A dermoscopic photograph of a skin lesion:
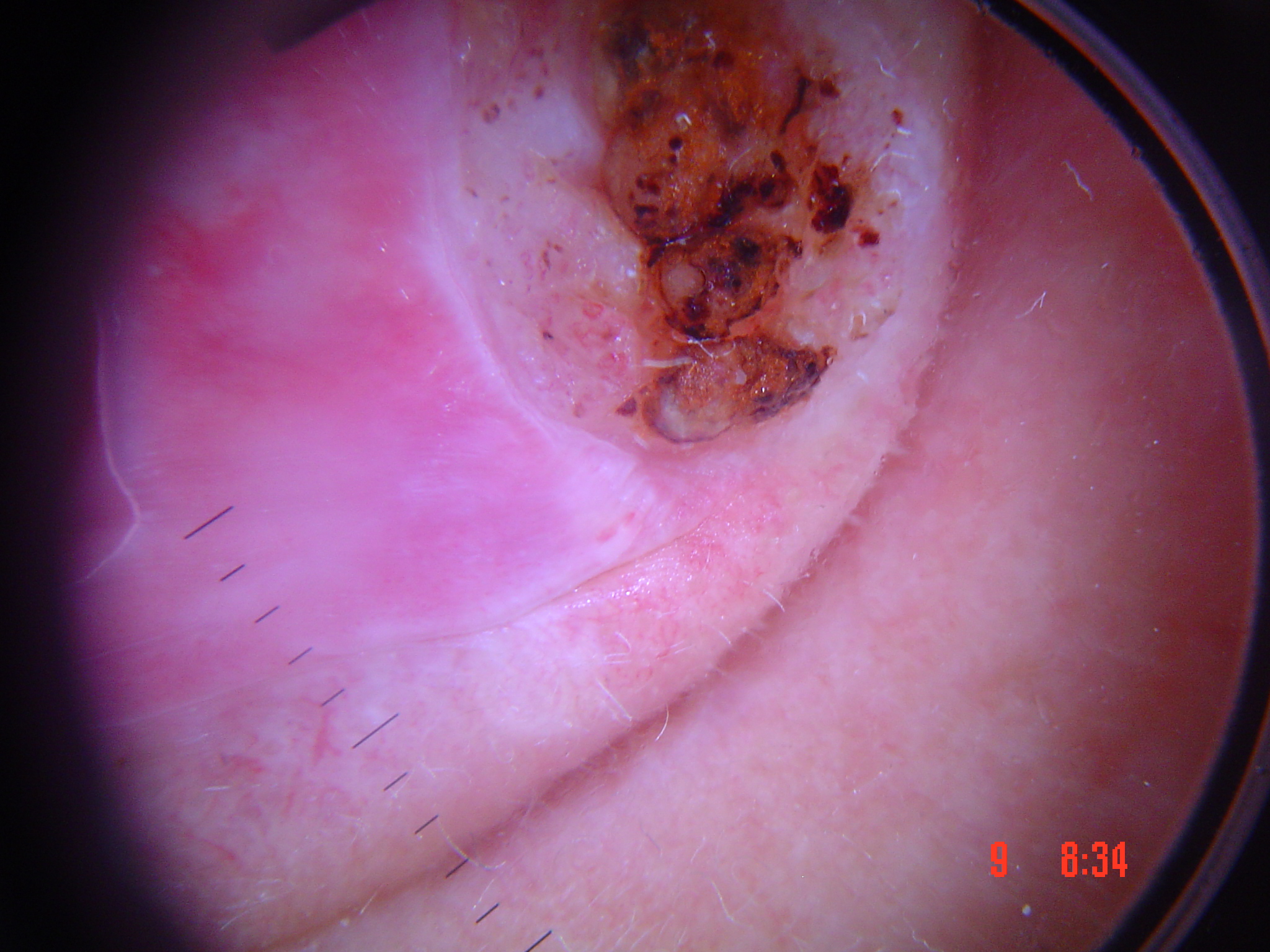| feature | finding |
|---|---|
| subtype | keratinocytic |
| diagnosis | squamous cell carcinoma (biopsy-proven) |